The patient notes the condition has been present for one to four weeks. Self-categorized by the patient as a rash. The lesion involves the leg. The contributor is 40–49, female. The photo was captured at an angle.
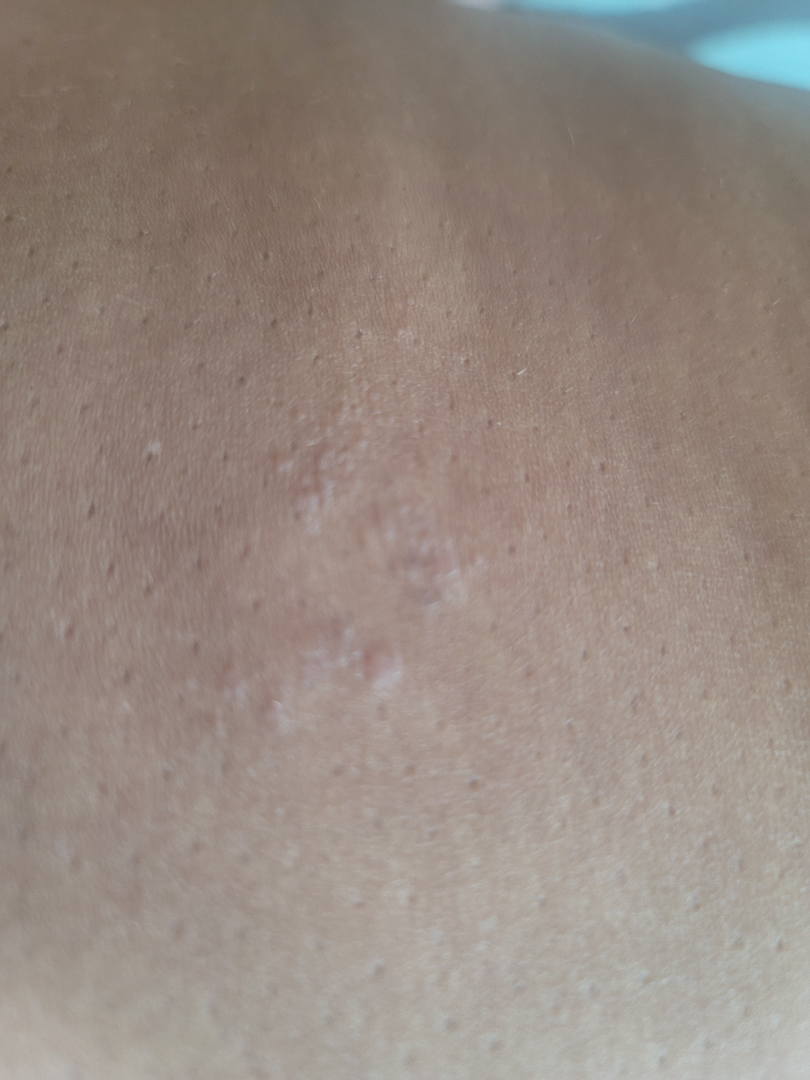differential:
  leading:
    - Eczema
  considered:
    - Verruca vulgaris
    - Epidermal nevus
    - SK/ISK